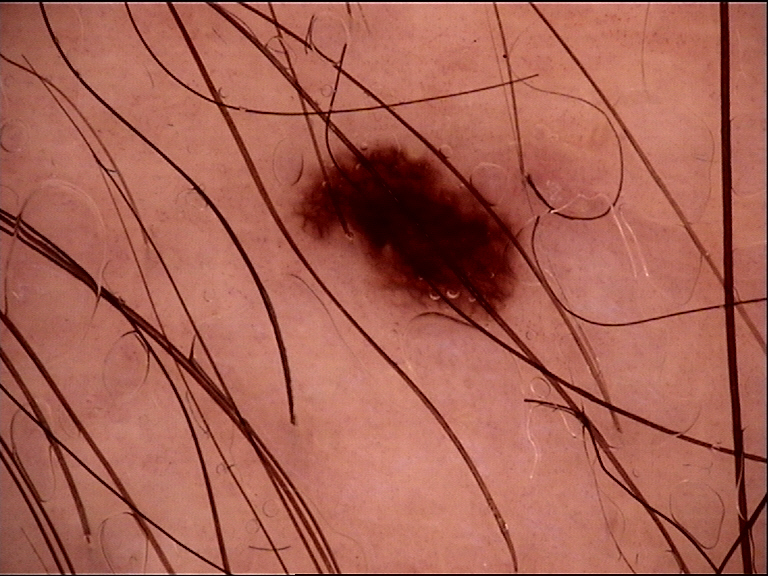Case: Dermoscopy of a skin lesion. Impression: The diagnostic label was a banal lesion — a junctional nevus.